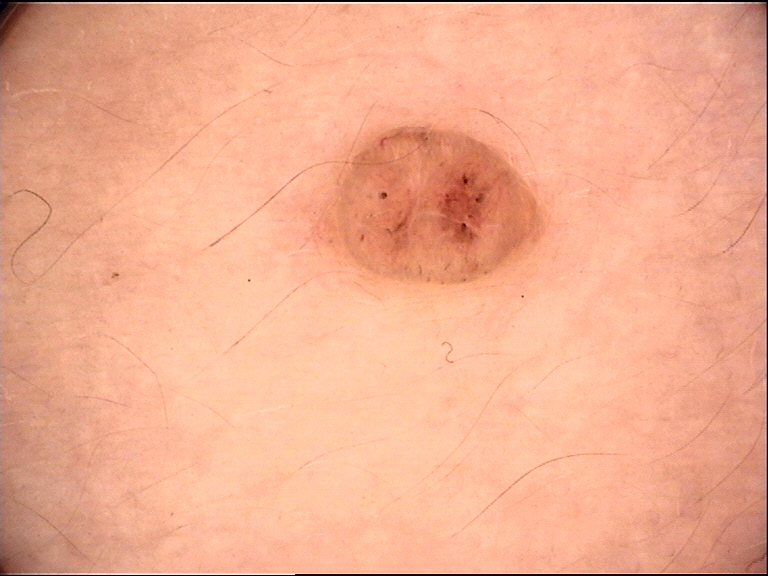  image: dermoscopy
  lesion_type:
    main_class: banal
    pattern: dermal
  diagnosis:
    name: dermal nevus
    code: db
    malignancy: benign
    super_class: melanocytic
    confirmation: expert consensus